The front of the torso is involved · the subject is male · the photo was captured at an angle: 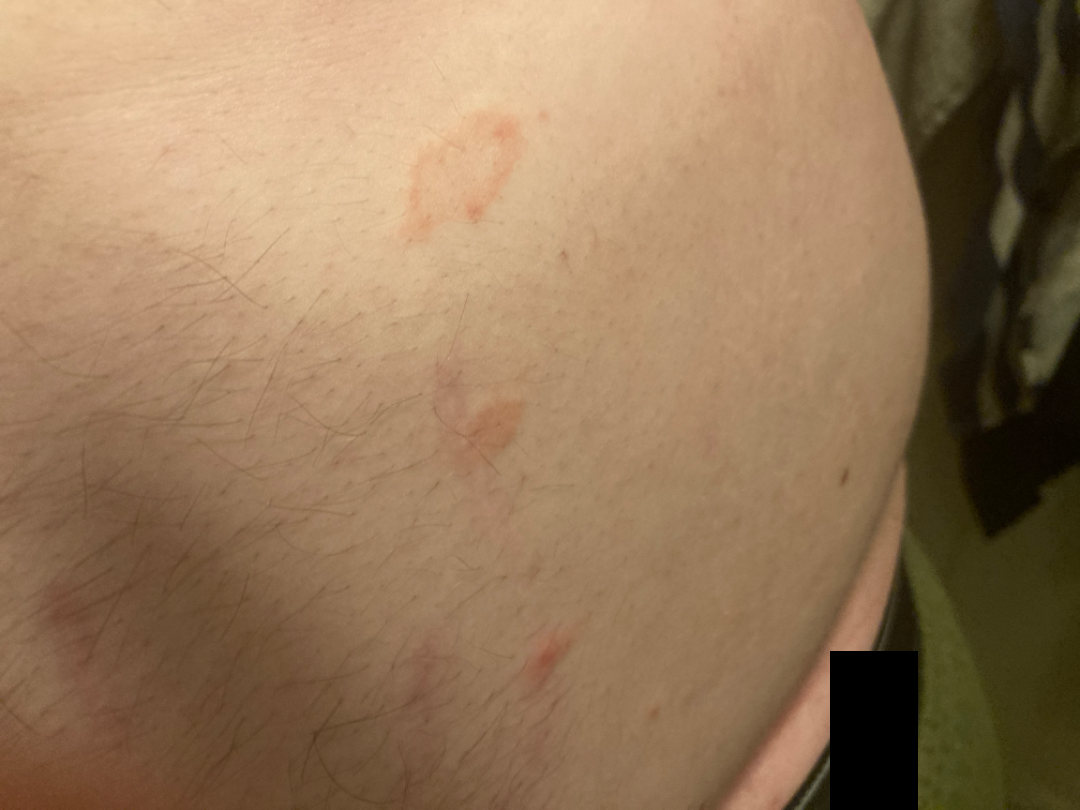| feature | finding |
|---|---|
| differential diagnosis | Pityriasis rosea (primary); Tinea (considered); Psoriasis (lower probability); Eczema (lower probability) |